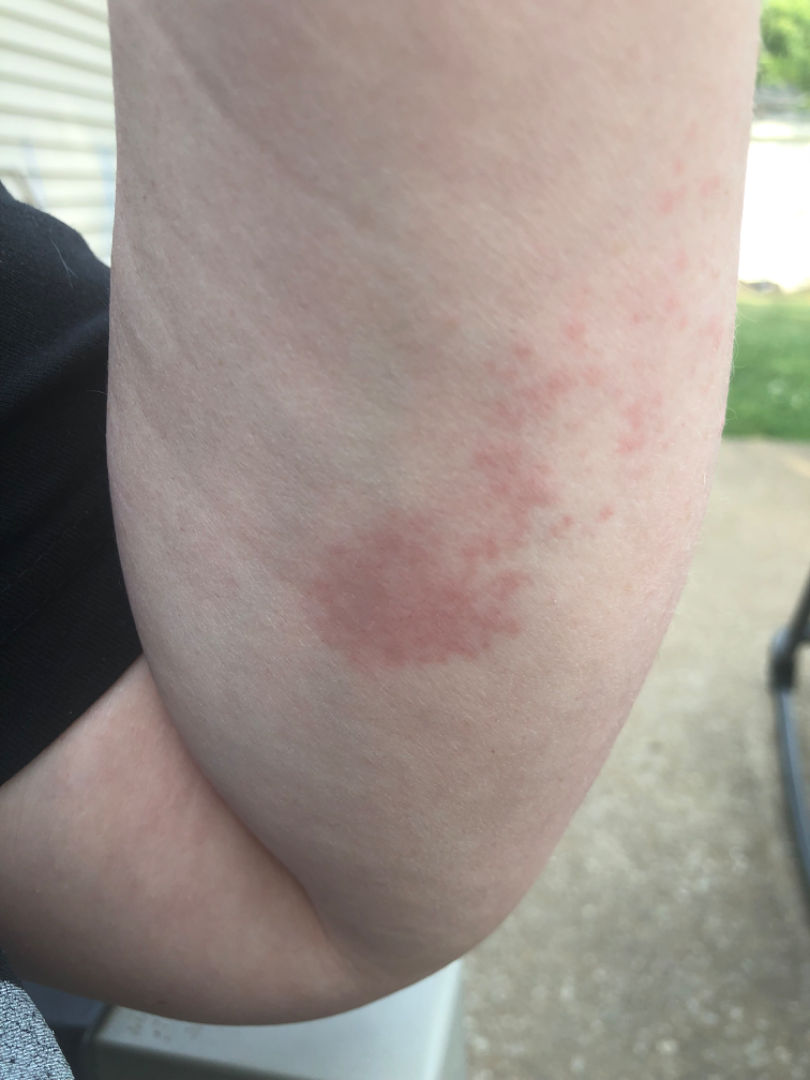Notes:
- shot type: close-up
- dermatologist impression: the leading consideration is Allergic Contact Dermatitis; also consider Eczema